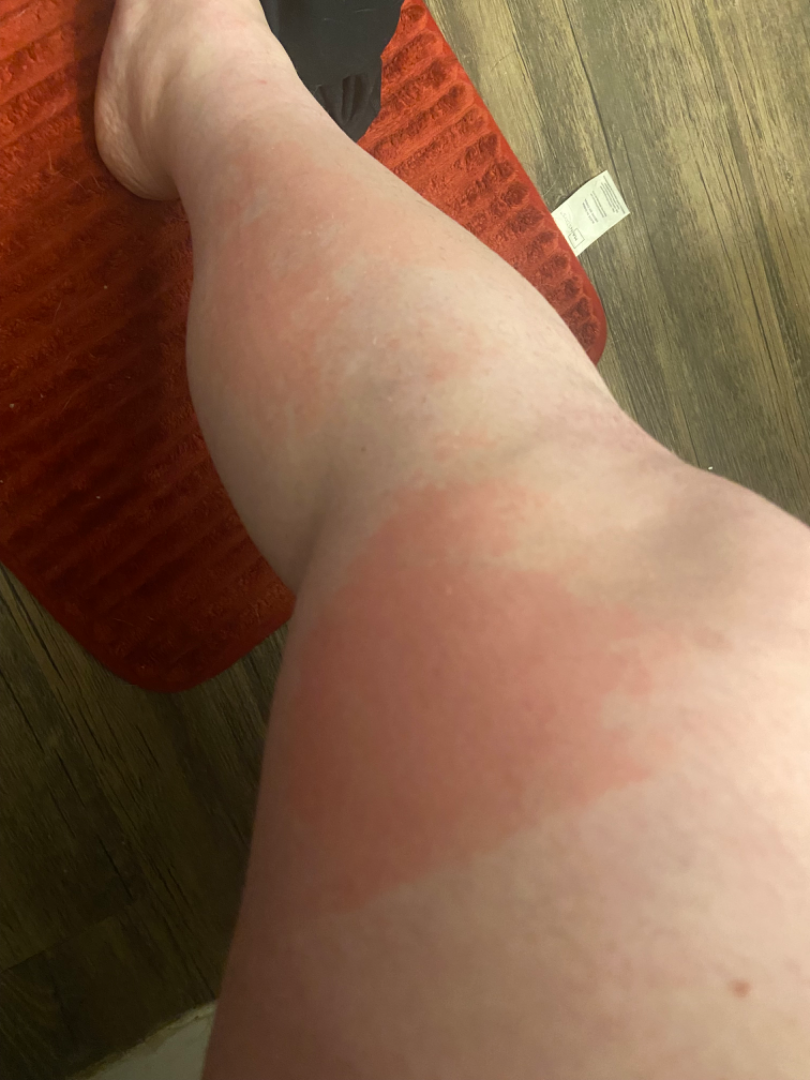The case was difficult to assess from the available photograph. Reported duration is less than one week. Female contributor, age 18–29. The contributor reports the lesion is flat. Symptoms reported: itching, enlargement, pain and burning. Located on the arm and leg. The patient considered this a rash. The photograph is a close-up of the affected area. Associated systemic symptoms include fatigue and chills.